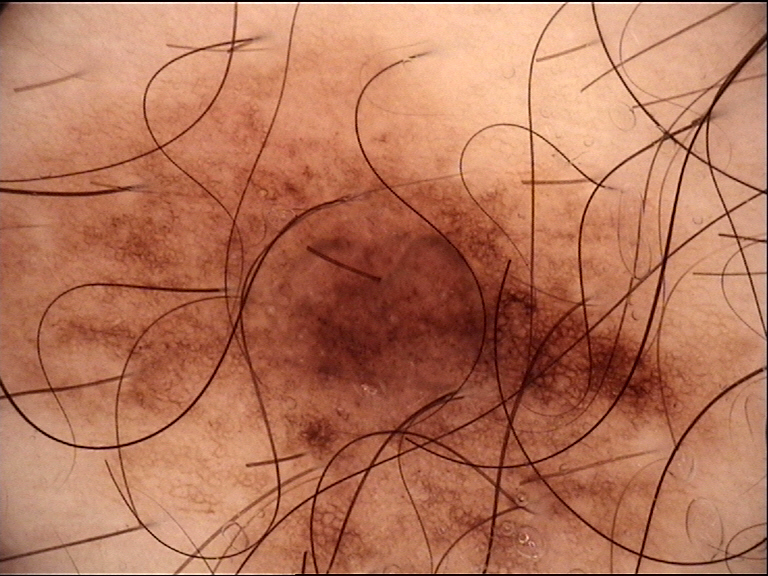diagnostic label: dysplastic junctional nevus (expert consensus).